A dermoscopic image of a skin lesion, a male patient aged approximately 55: 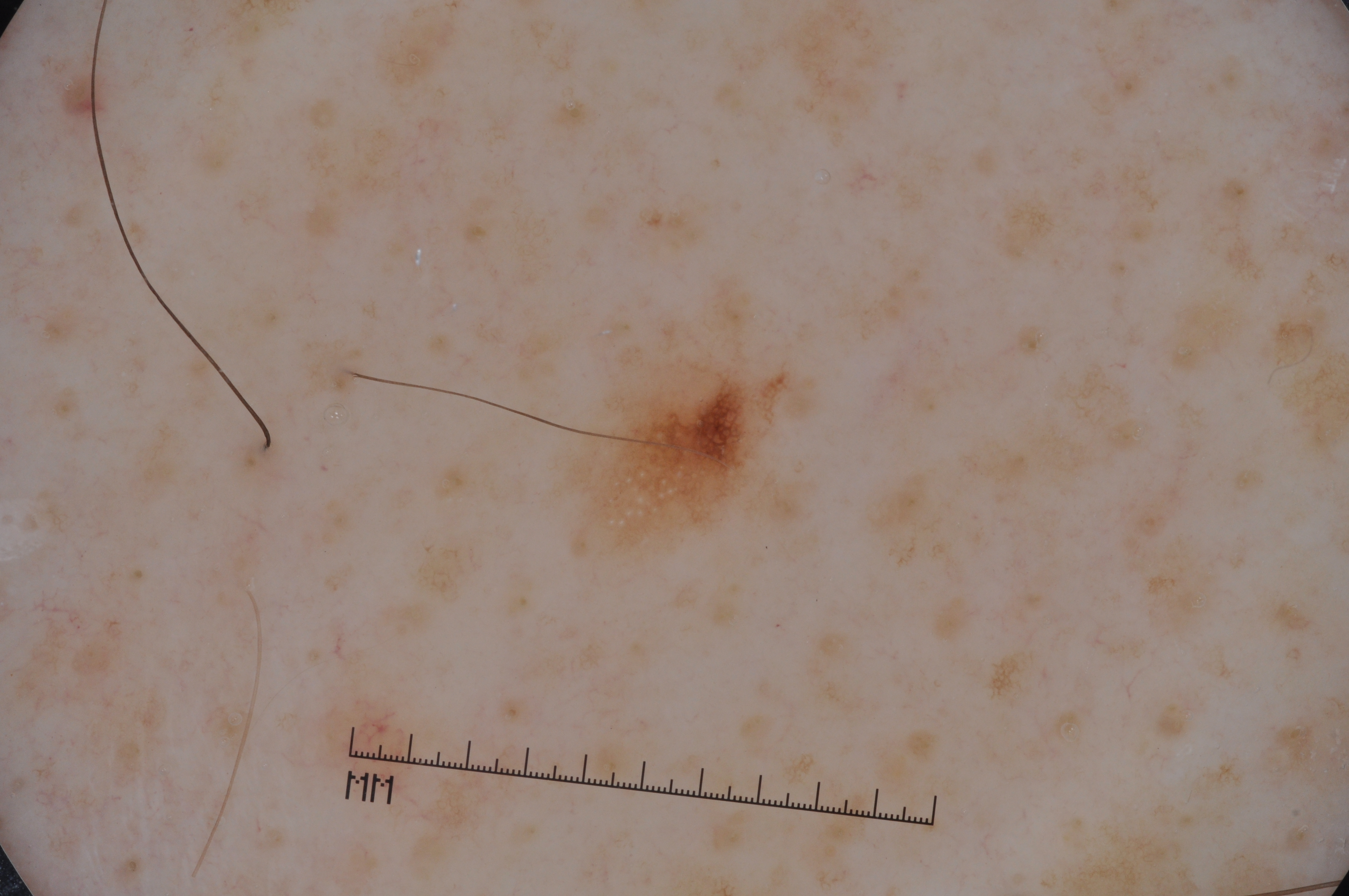Dermoscopic review identifies milia-like cysts and pigment network; no negative network or streaks. With coordinates (x1, y1, x2, y2), the lesion is bounded by 545, 350, 796, 565. A small lesion occupying a minor part of the field. Diagnosed as a melanocytic nevus.